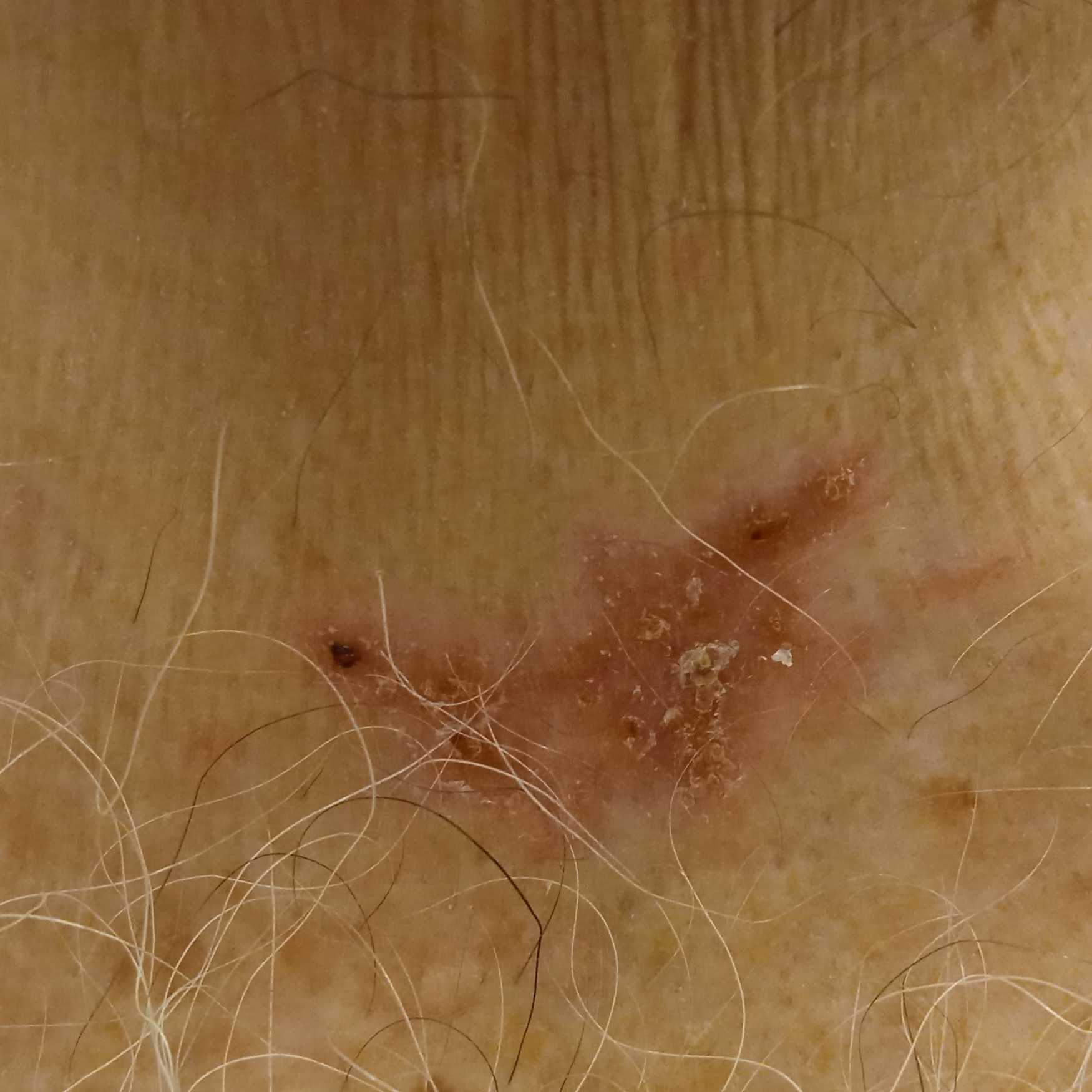The patient describes having few moles overall. Referred with a clinical suspicion of basal cell carcinoma. The patient says their skin tans without first burning. A male subject 67 years of age. A clinical photograph of a skin lesion. The patient reports a personal history of skin cancer. The lesion is about 19 mm across. On biopsy, the diagnosis was a basal cell carcinoma, following a punch biopsy, with a measured thickness of 0.8 mm.